A patient 65 years of age · a clinical photo of a skin lesion taken with a smartphone — 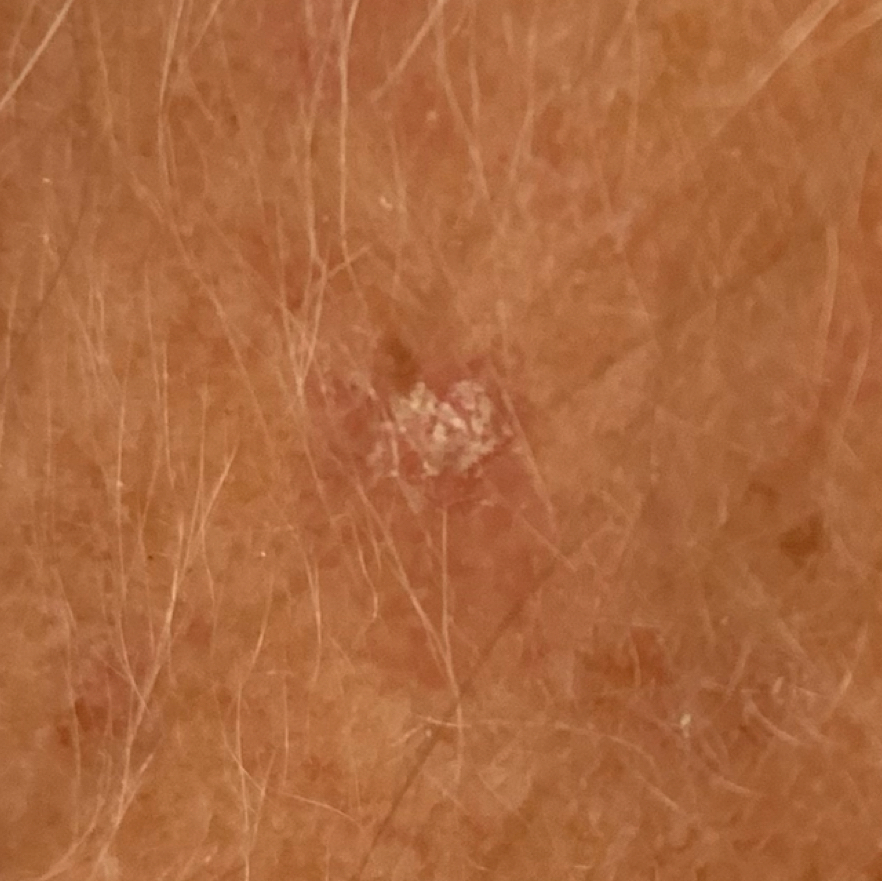Q: Where on the body is the lesion?
A: the face
Q: Any reported symptoms?
A: itching
Q: What was the clinical impression?
A: actinic keratosis (clinical consensus)